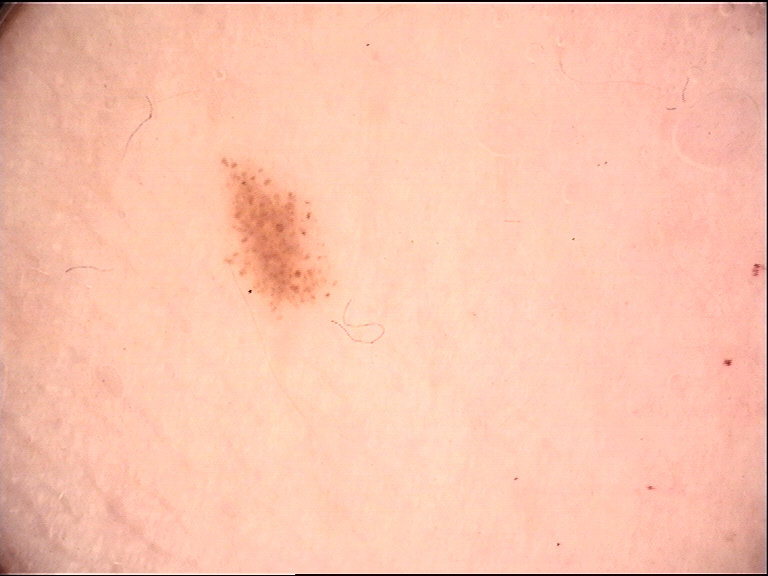<case>
  <image>dermoscopy</image>
  <diagnosis>
    <name>acral dysplastic junctional nevus</name>
    <code>ajd</code>
    <malignancy>benign</malignancy>
    <super_class>melanocytic</super_class>
    <confirmation>expert consensus</confirmation>
  </diagnosis>
</case>